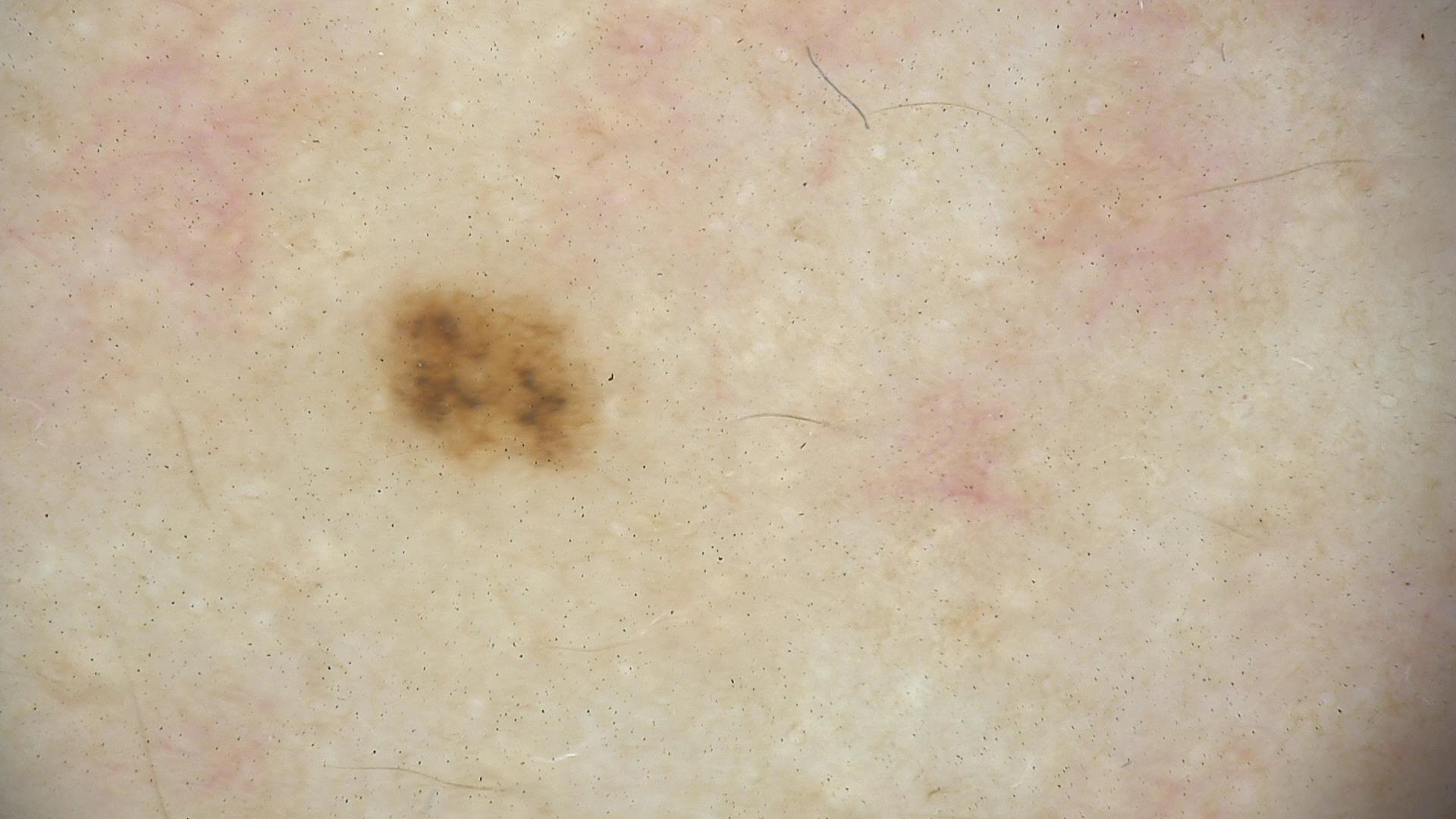A dermoscopy image of a single skin lesion.
Classified as a dysplastic junctional nevus.